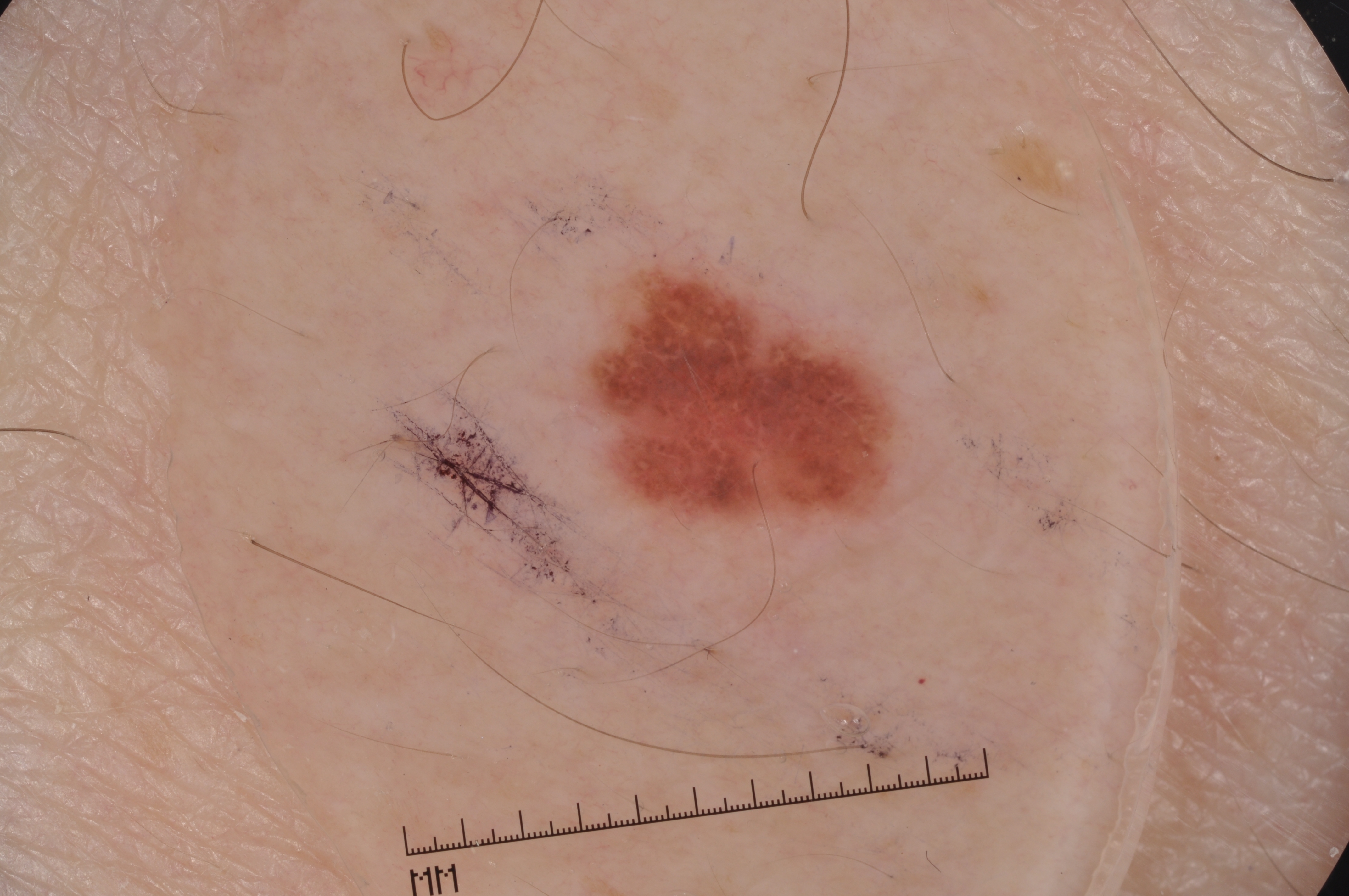Q: What is the imaging modality?
A: dermoscopy of a skin lesion
Q: What are the patient's age and sex?
A: male, aged approximately 70
Q: Where is the lesion in the image?
A: 590 273 896 525
Q: Lesion extent?
A: ~5% of the field
Q: Which dermoscopic features were noted?
A: negative network
Q: What is the diagnosis?
A: a melanocytic nevus